The affected area is the leg; a close-up photograph; female patient, age 18–29:
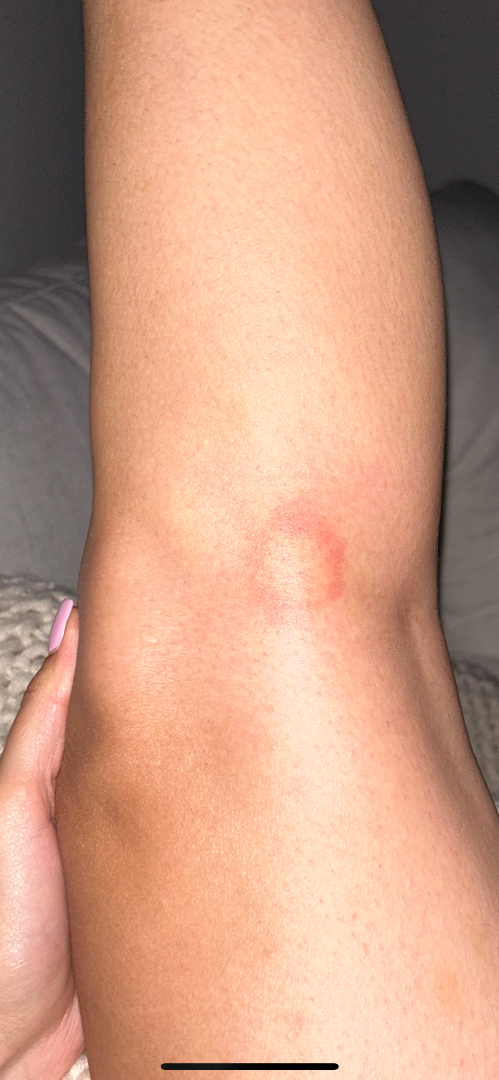Case summary:
– assessment: indeterminate